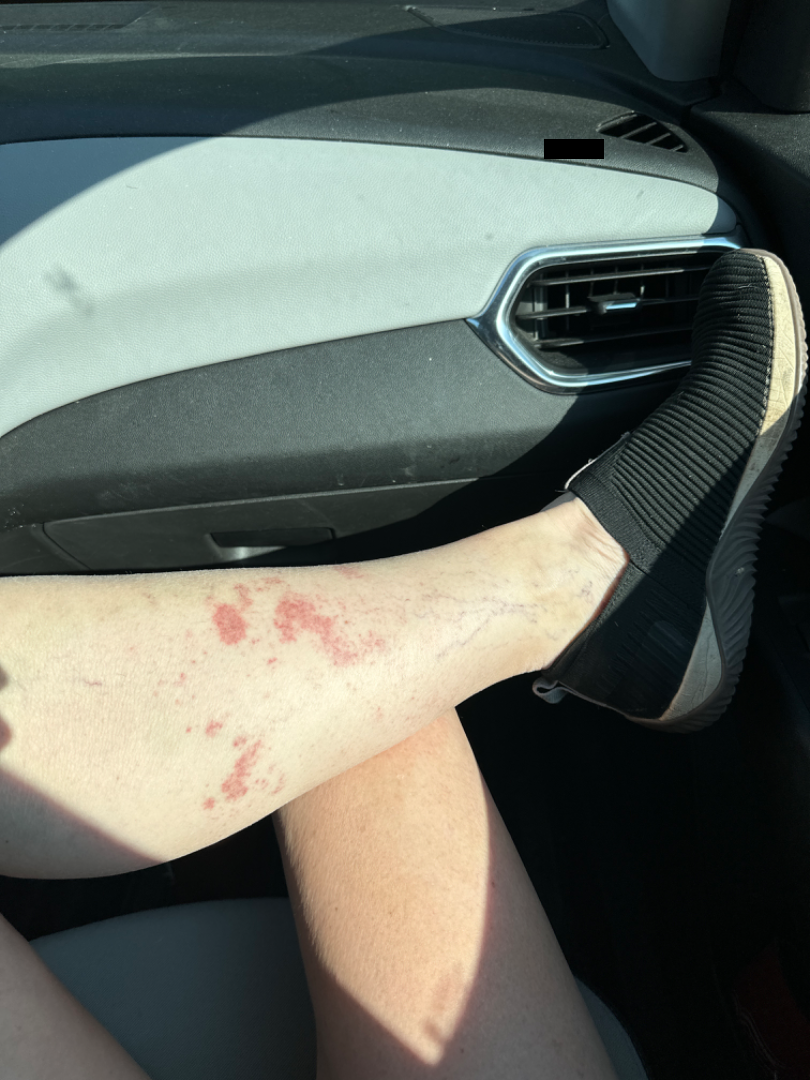Assessment: Favoring Pigmented purpuric eruption; the differential also includes Leukocytoclastic Vasculitis; a more distant consideration is Allergic Contact Dermatitis.